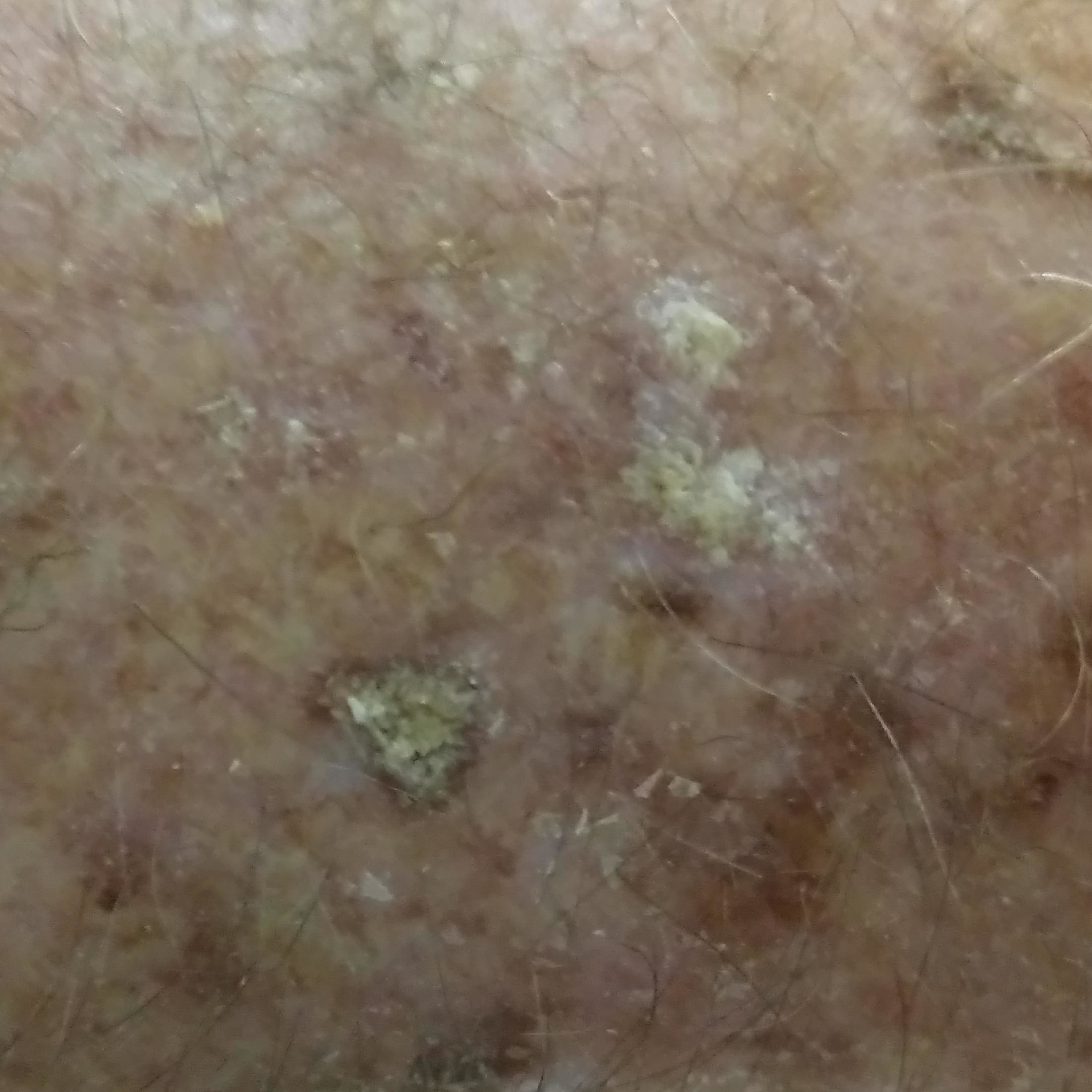patient: 77 years of age | image type: clinical photograph | body site: a forearm | patient-reported symptoms: none reported | assessment: actinic keratosis (clinical consensus).